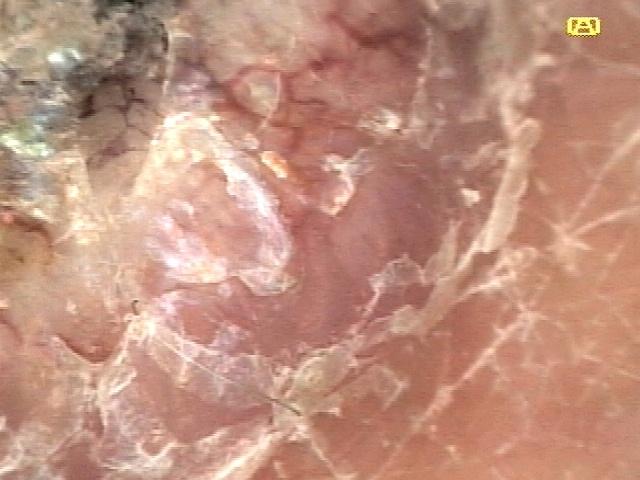Summary:
A female patient in their mid-70s. Recorded as Fitzpatrick skin type II. The chart documents a prior melanoma. A dermoscopic image of a skin lesion. Located on a lower extremity.
Diagnosis:
Histopathology confirmed an epidermal proliferation — a squamous cell carcinoma.